Close-up view; located on the arm; the patient reported no systemic symptoms; the patient reports the lesion is raised or bumpy; the condition has been present for less than one week.
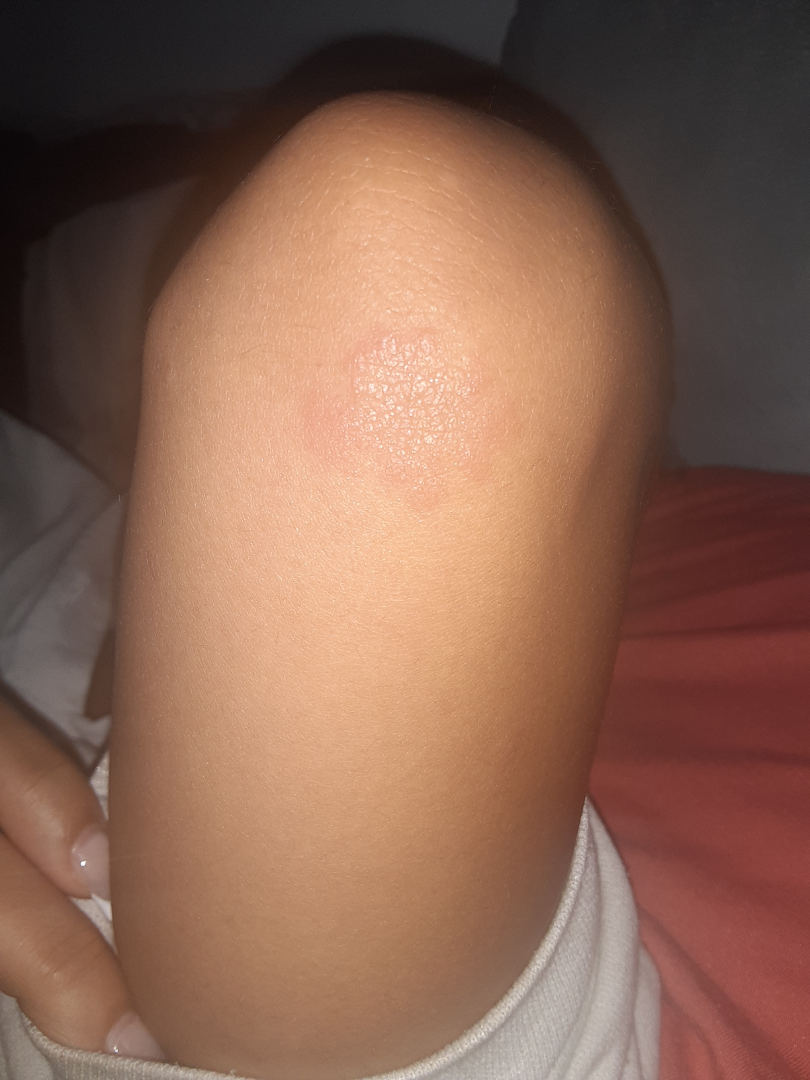assessment: Chronic dermatitis, NOS (favored).